Close-up view:
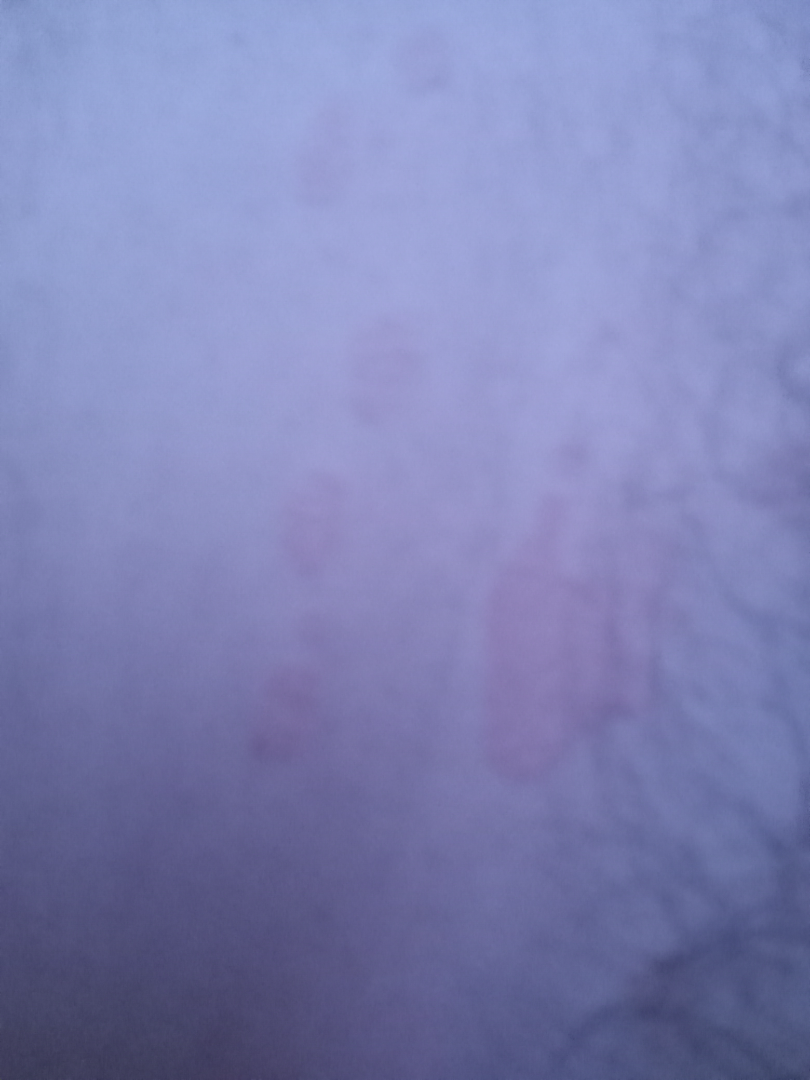The case was difficult to assess from the available photograph.